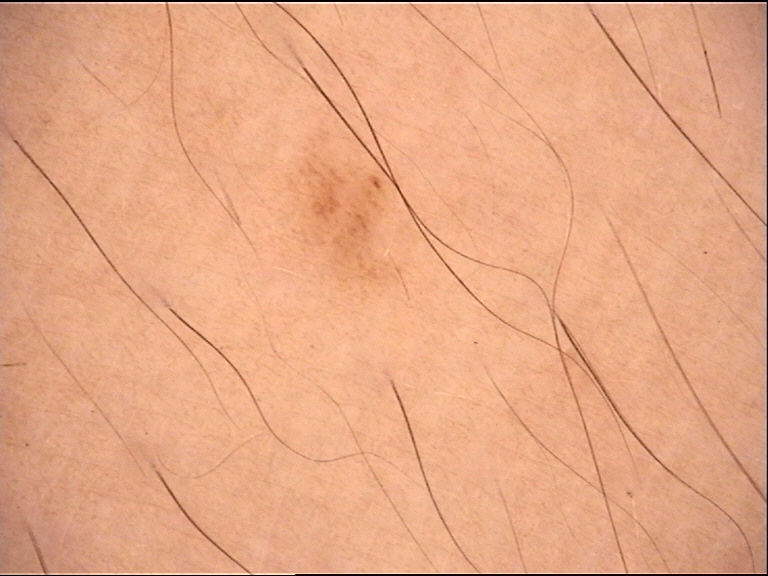Impression: The diagnostic label was a dysplastic junctional nevus.